A skin lesion imaged with a dermatoscope: 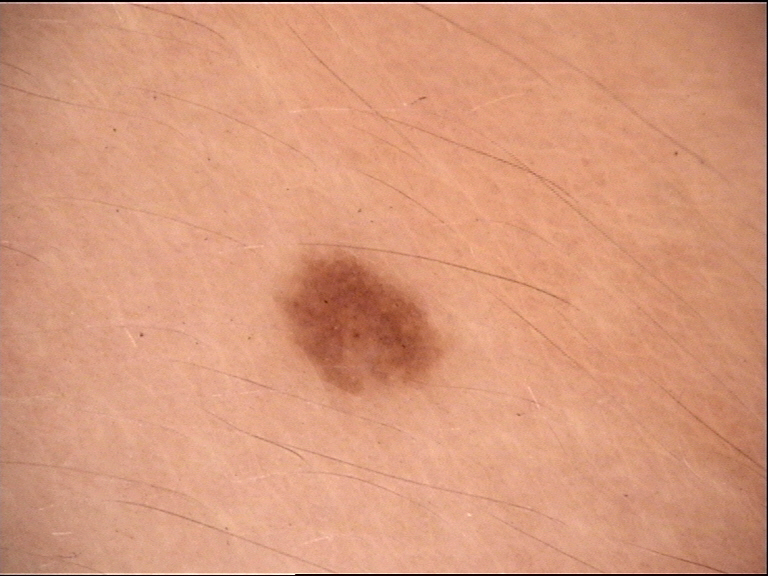The architecture is that of a banal lesion. The diagnosis was a junctional nevus.